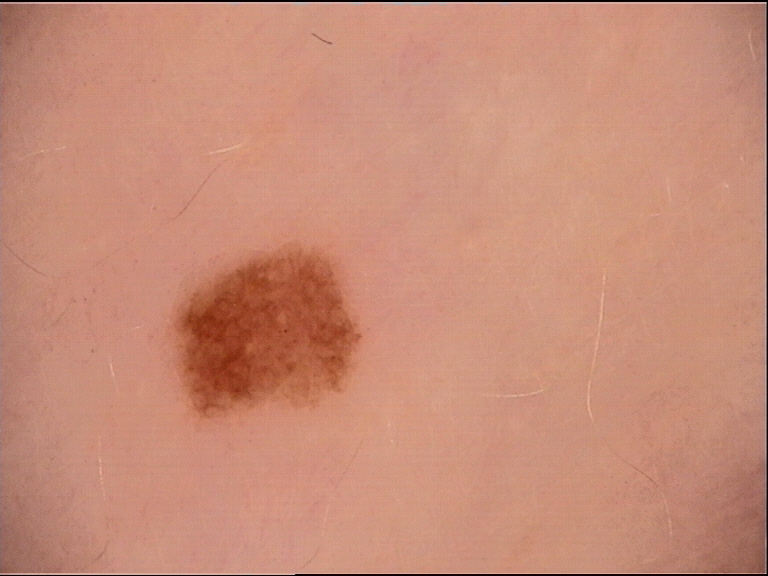{"image": "dermoscopy", "lesion_type": {"main_class": "banal", "pattern": "junctional"}, "diagnosis": {"name": "junctional nevus", "code": "jb", "malignancy": "benign", "super_class": "melanocytic", "confirmation": "expert consensus"}}